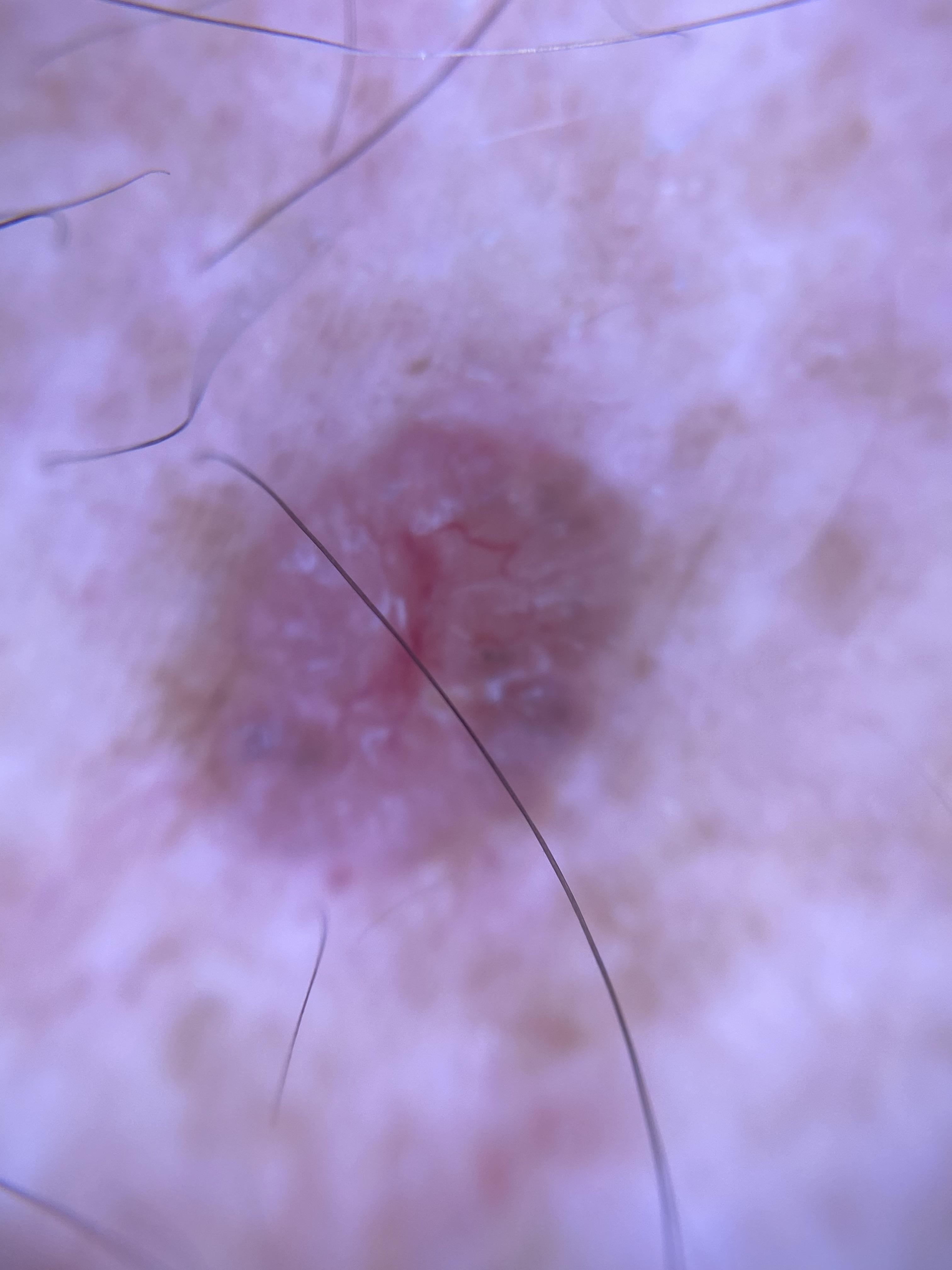<case>
<image>dermoscopic image</image>
<patient>
<age_approx>75</age_approx>
<sex>male</sex>
</patient>
<lesion_location>
<region>the trunk</region>
<detail>the posterior trunk</detail>
</lesion_location>
<diagnosis>
<name>Basal cell carcinoma</name>
<malignancy>malignant</malignancy>
<confirmation>histopathology</confirmation>
<lineage>adnexal</lineage>
</diagnosis>
</case>